The arm and head or neck are involved; the photo was captured at a distance:
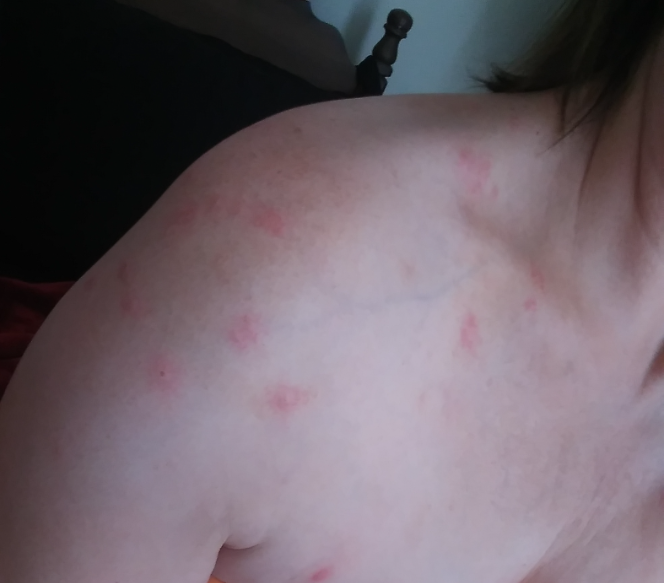The lesion is described as raised or bumpy. Reported lesion symptoms include itching. Skin tone: Fitzpatrick skin type II; non-clinician graders estimated 2 on the MST. The reviewing clinician's impression was: Insect Bite (1.00).